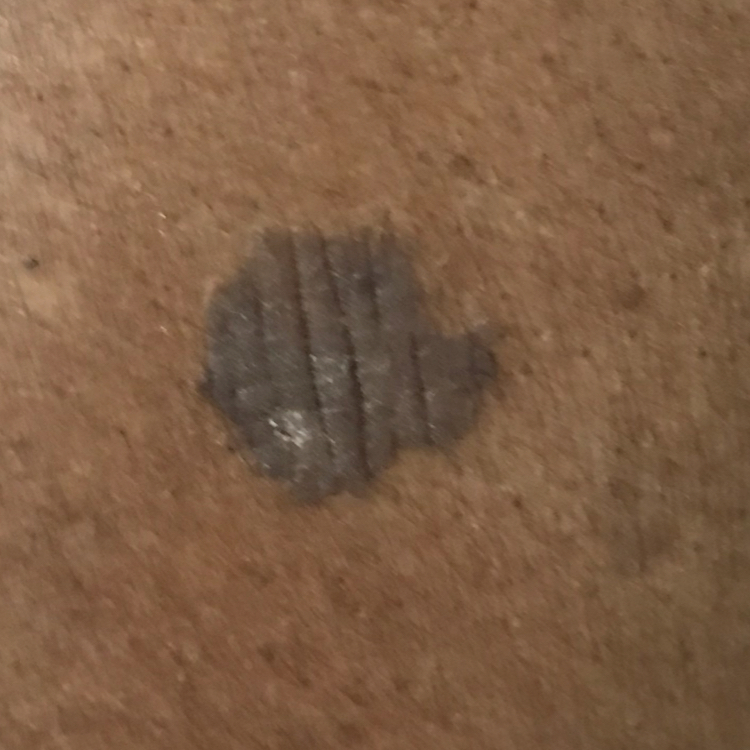A female subject aged 67. History notes tobacco use and pesticide exposure. The lesion measures approximately 15 × 15 mm. The patient reports that the lesion is elevated. Confirmed on histopathology as a seborrheic keratosis.